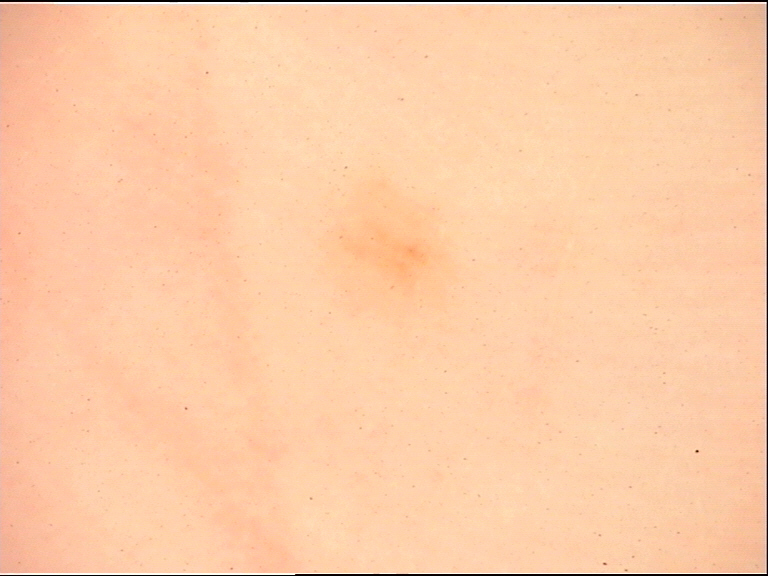Impression: The diagnosis was an acral junctional nevus.